A contact-polarized dermoscopy image of a skin lesion · a male subject about 45 years old · the patient was assessed as Fitzpatrick skin type II · the chart notes no melanoma in first-degree relatives and no prior melanoma: 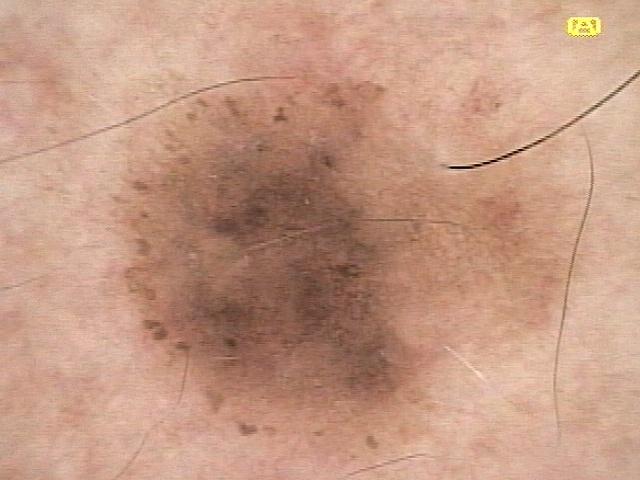{
  "lesion_location": {
    "region": "the trunk",
    "detail": "the posterior trunk"
  },
  "diagnosis": {
    "name": "Nevus",
    "malignancy": "benign",
    "confirmation": "histopathology",
    "lineage": "melanocytic"
  }
}